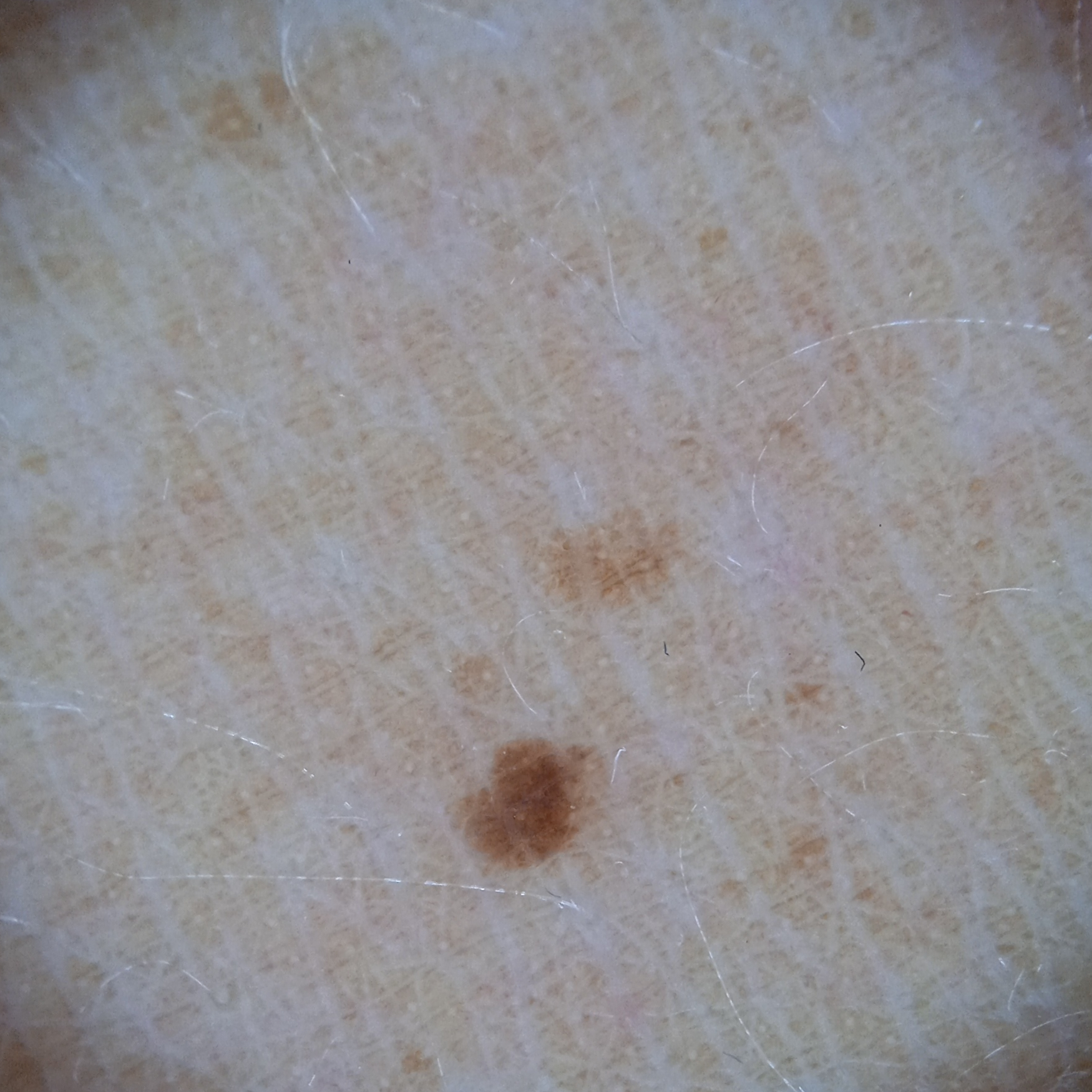A female subject aged 47. Acquired for a research image collection, with no referral diagnosis. A dermoscopic image of a skin lesion. The lesion is on the back. The lesion measures approximately 1.8 mm. The consensus diagnosis for this lesion was a melanocytic nevus.